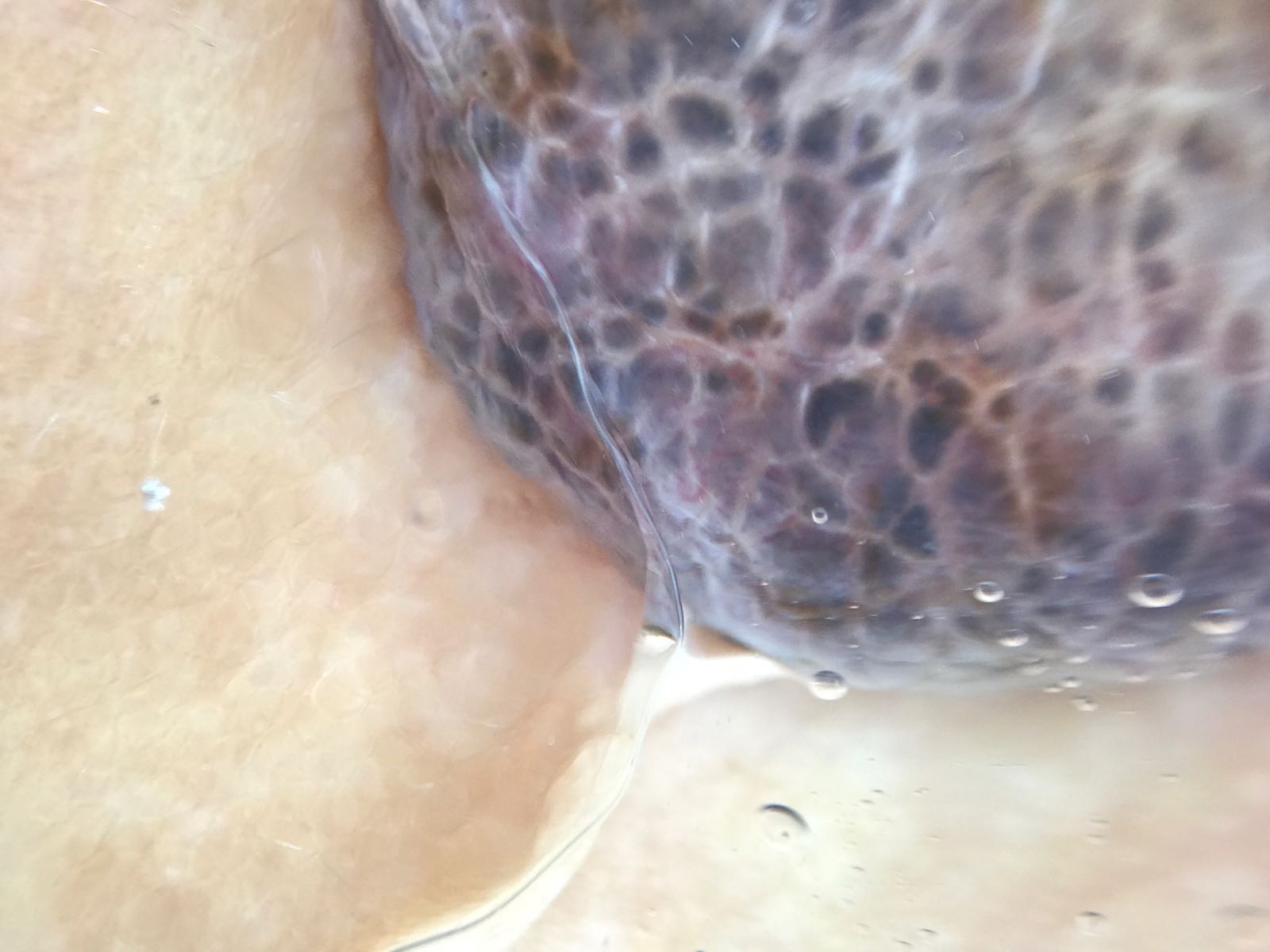A dermatoscopic image of a skin lesion.
The biopsy diagnosis was a malignant lesion — a melanoma.